Present for about one day. Skin tone: Fitzpatrick phototype III; non-clinician graders estimated Monk skin tone scale 3 (US pool) or 2 (India pool). This is a close-up image. The lesion involves the leg:
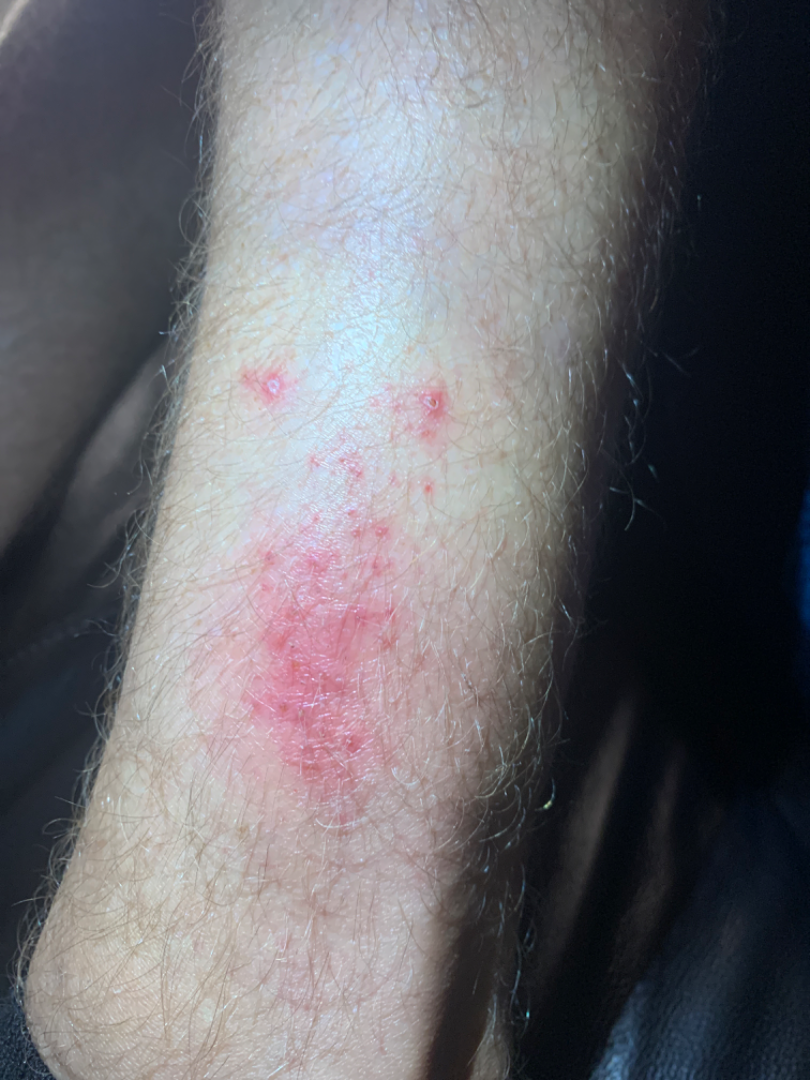{"assessment": "indeterminate"}